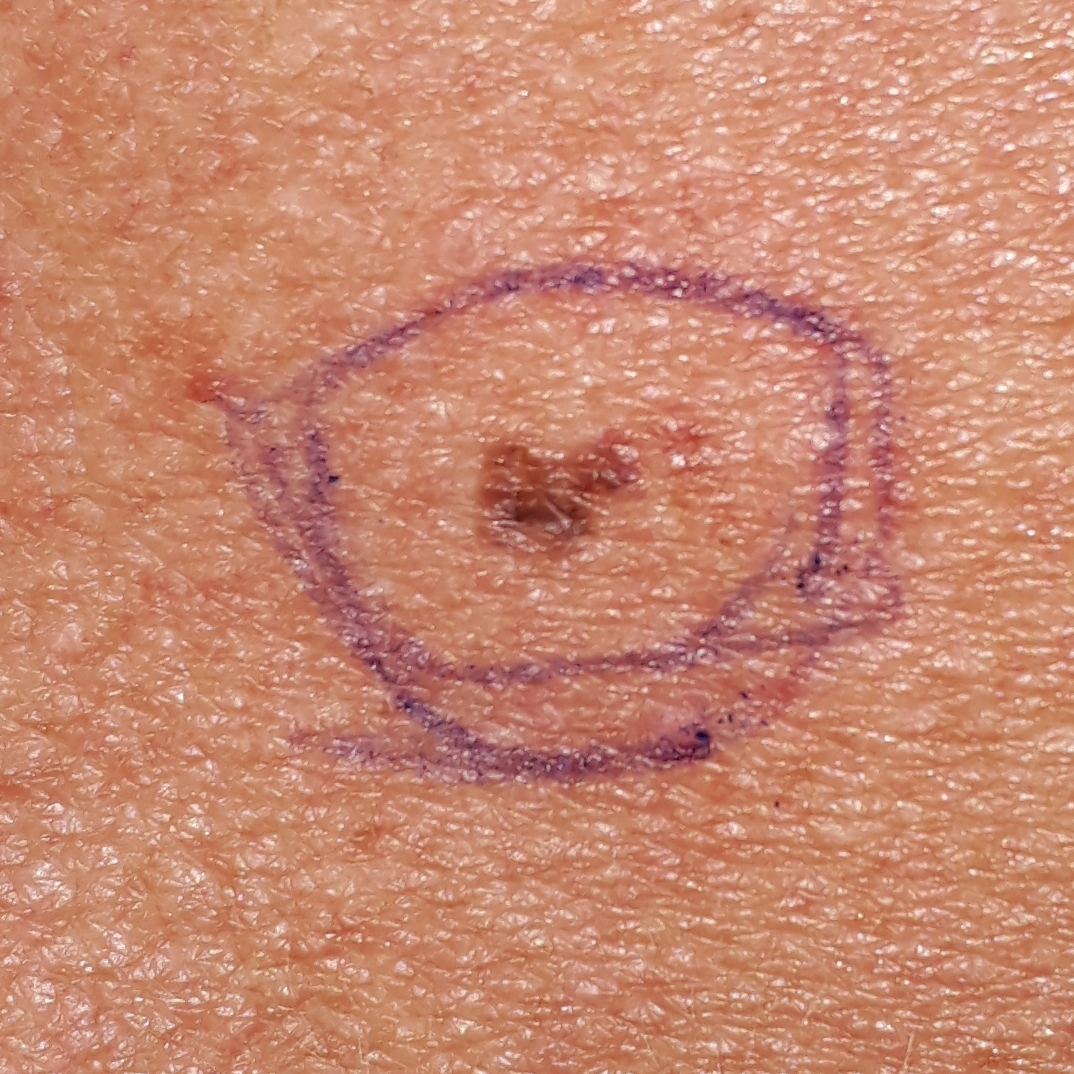Expert review favored a nevus.